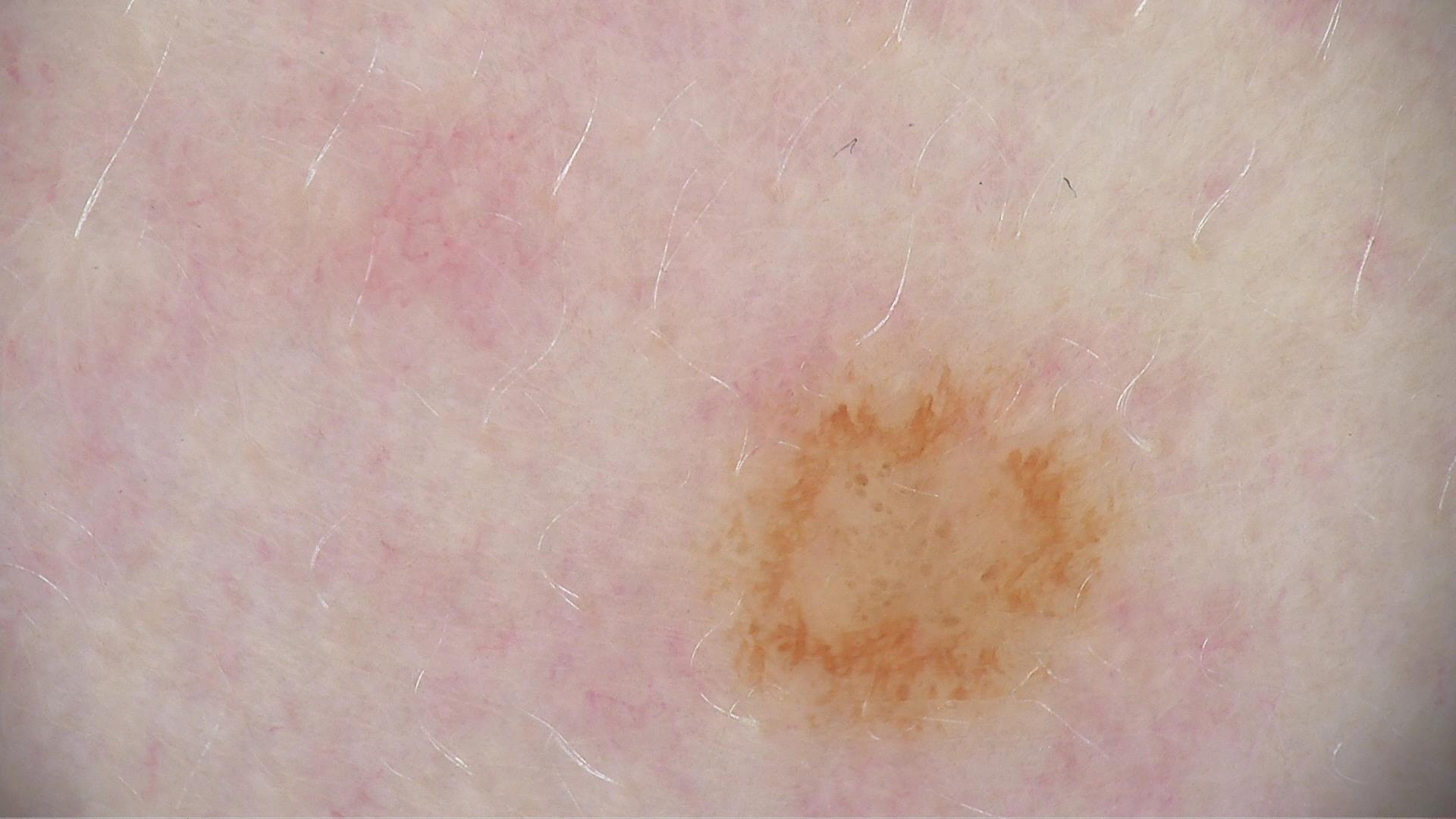<lesion>
  <diagnosis>
    <name>dysplastic junctional nevus</name>
    <code>jd</code>
    <malignancy>benign</malignancy>
    <super_class>melanocytic</super_class>
    <confirmation>expert consensus</confirmation>
  </diagnosis>
</lesion>